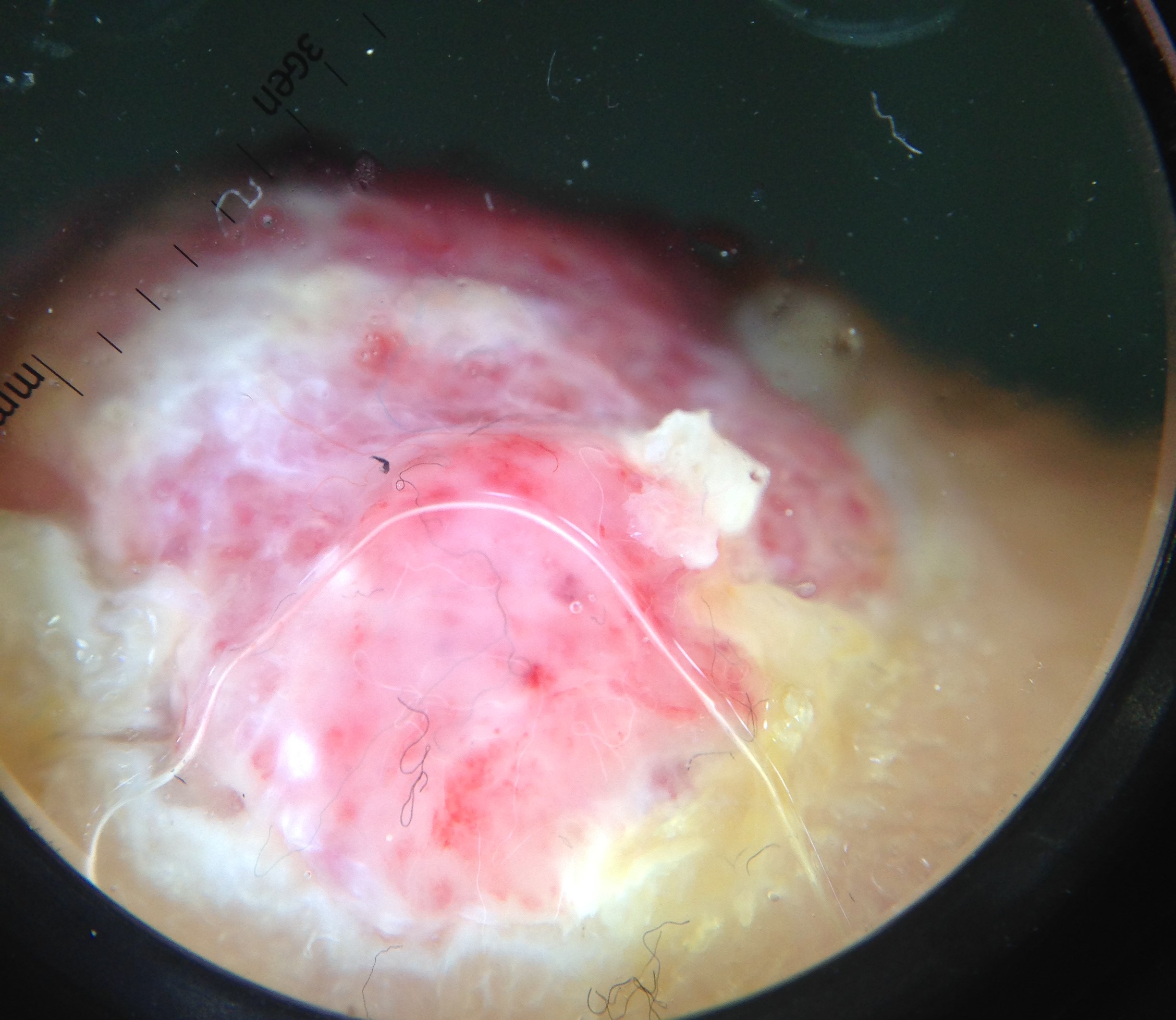{
  "diagnosis": {
    "name": "acral nodular melanoma",
    "code": "anm",
    "malignancy": "malignant",
    "super_class": "melanocytic",
    "confirmation": "histopathology"
  }
}